Texture is reported as raised or bumpy and fluid-filled. A close-up photograph. The patient considered this a rash. Located on the head or neck. The lesion is associated with pain, itching, bleeding, bothersome appearance and burning. The condition has been present for less than one week — 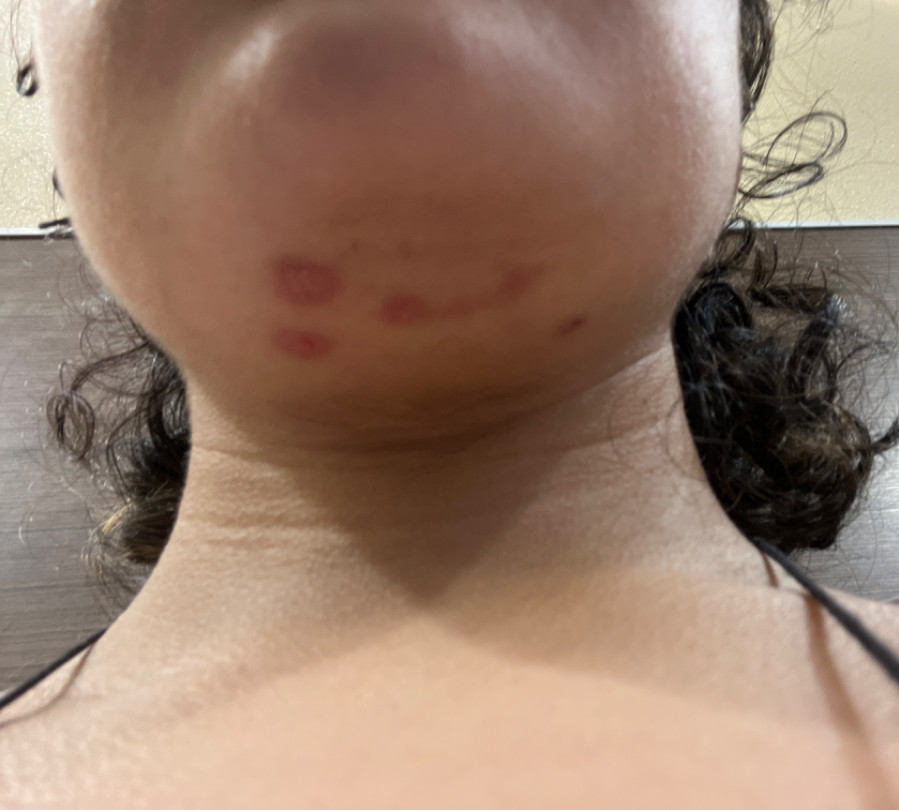The primary impression is Impetigo; also raised was Folliculitis.